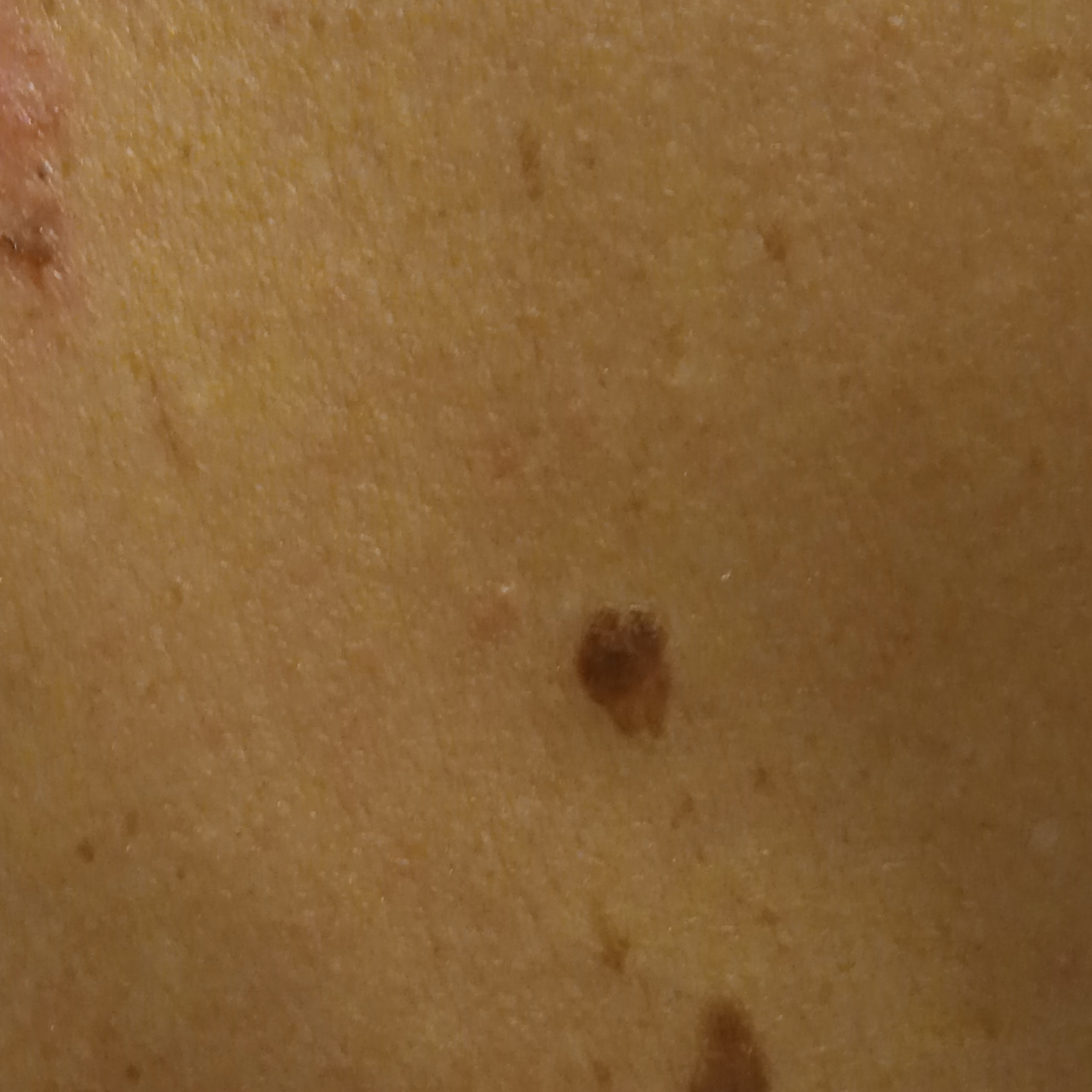Collected as part of a research study, without a referral diagnosis. The patient reports no family history of skin cancer. A clinical photograph of a skin lesion. The patient describes having a moderate number of moles. A male patient age 72. The patient says their skin tans without first burning. The lesion is located on the back. The lesion is about 9.6 mm across. The lesion was assessed as a seborrheic keratosis.